Imaged for a research study, with no referral diagnosis recorded.
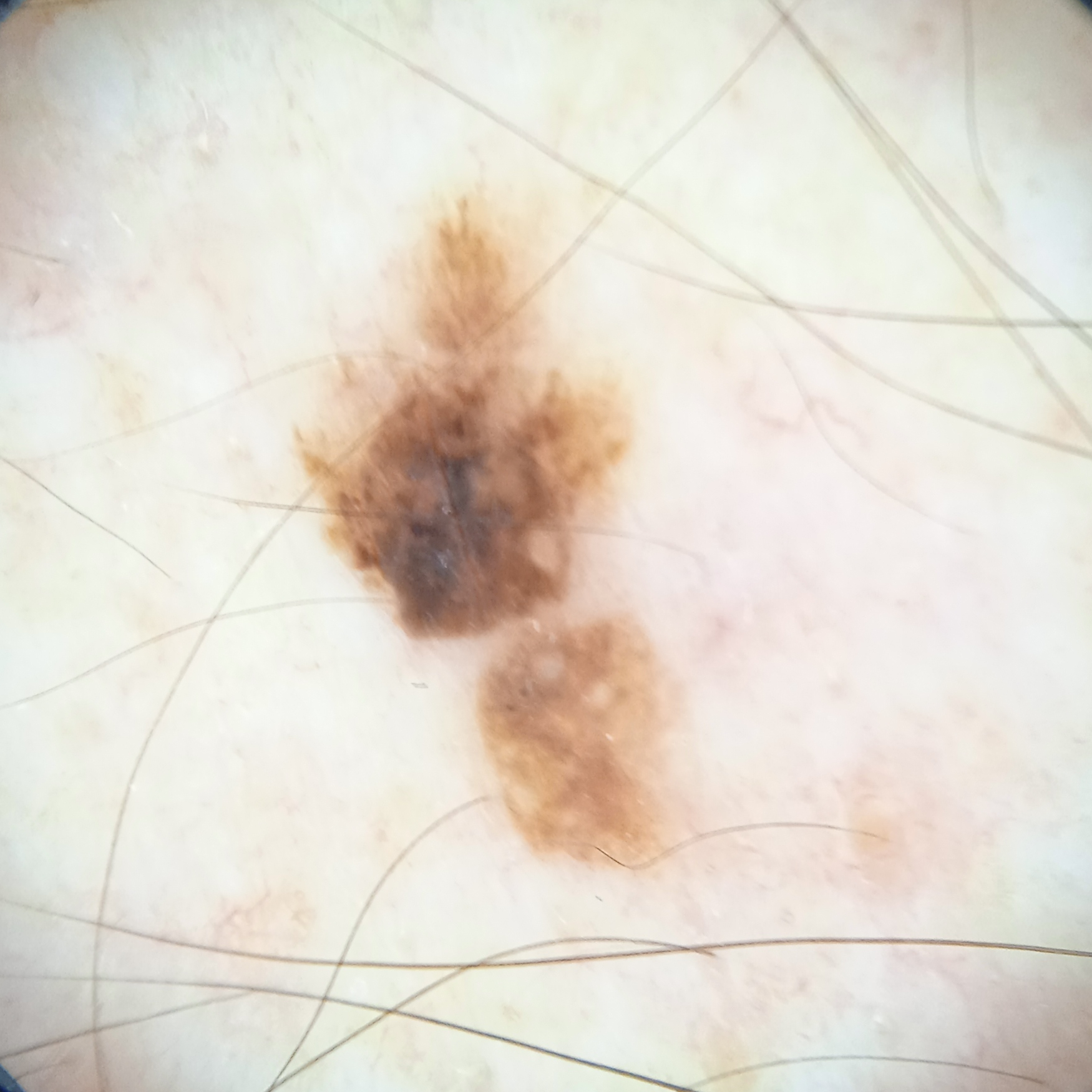| field | value |
|---|---|
| diameter | 7.8 mm |
| assessment | seborrheic keratosis (dermatologist consensus) |